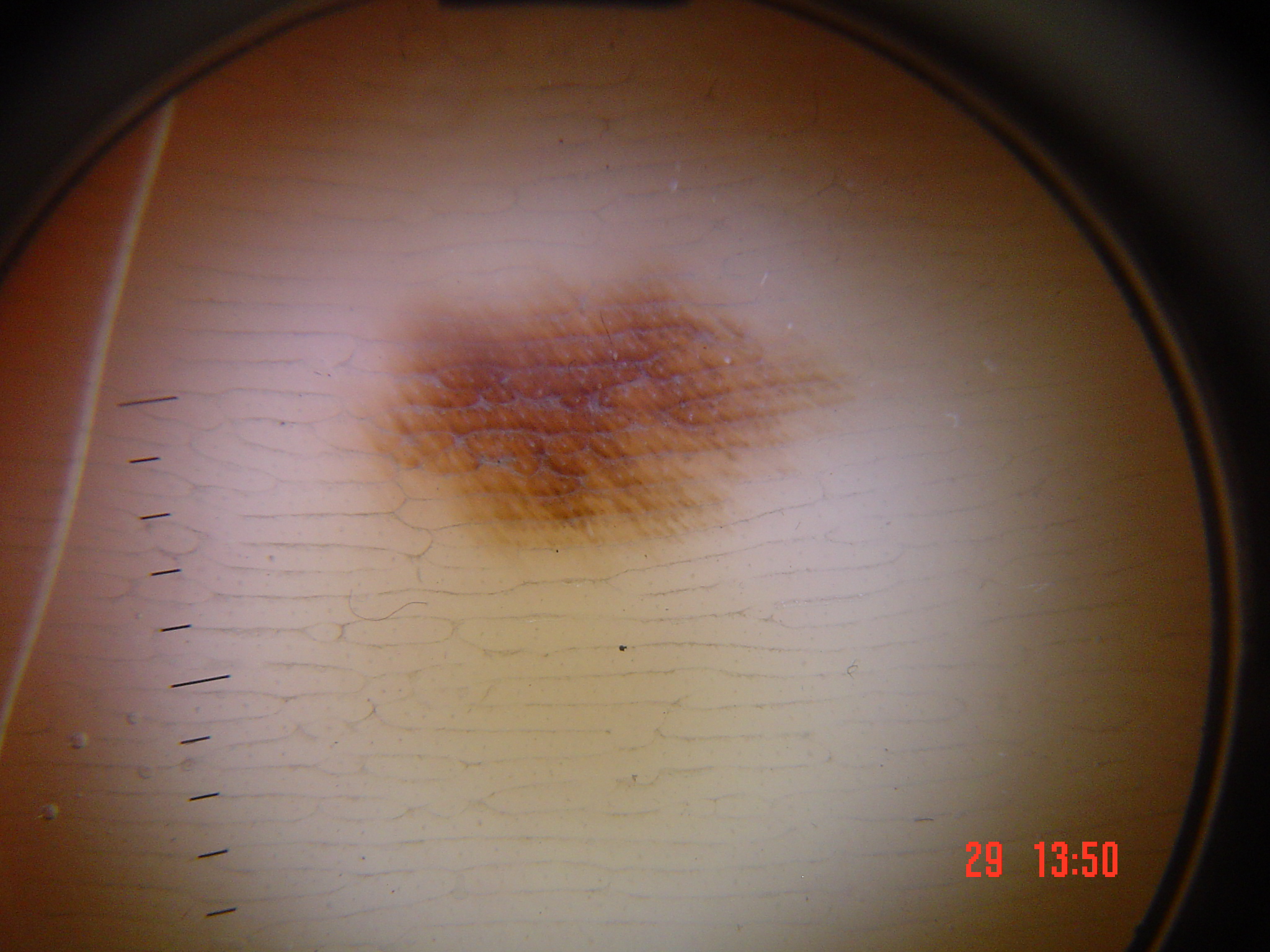| field | value |
|---|---|
| diagnosis | acral dysplastic junctional nevus (expert consensus) |